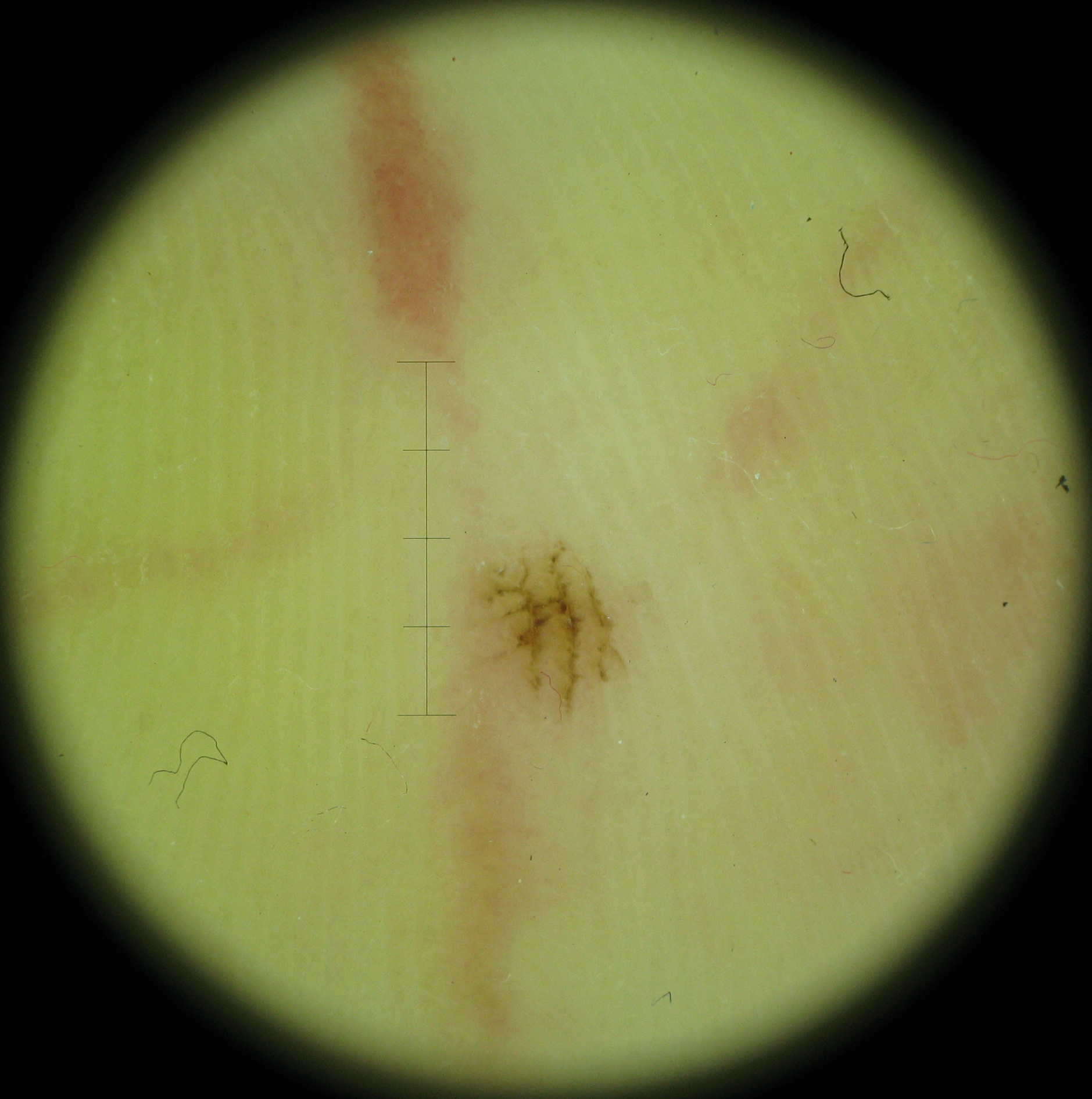classification = banal; diagnosis = acral junctional nevus (expert consensus).